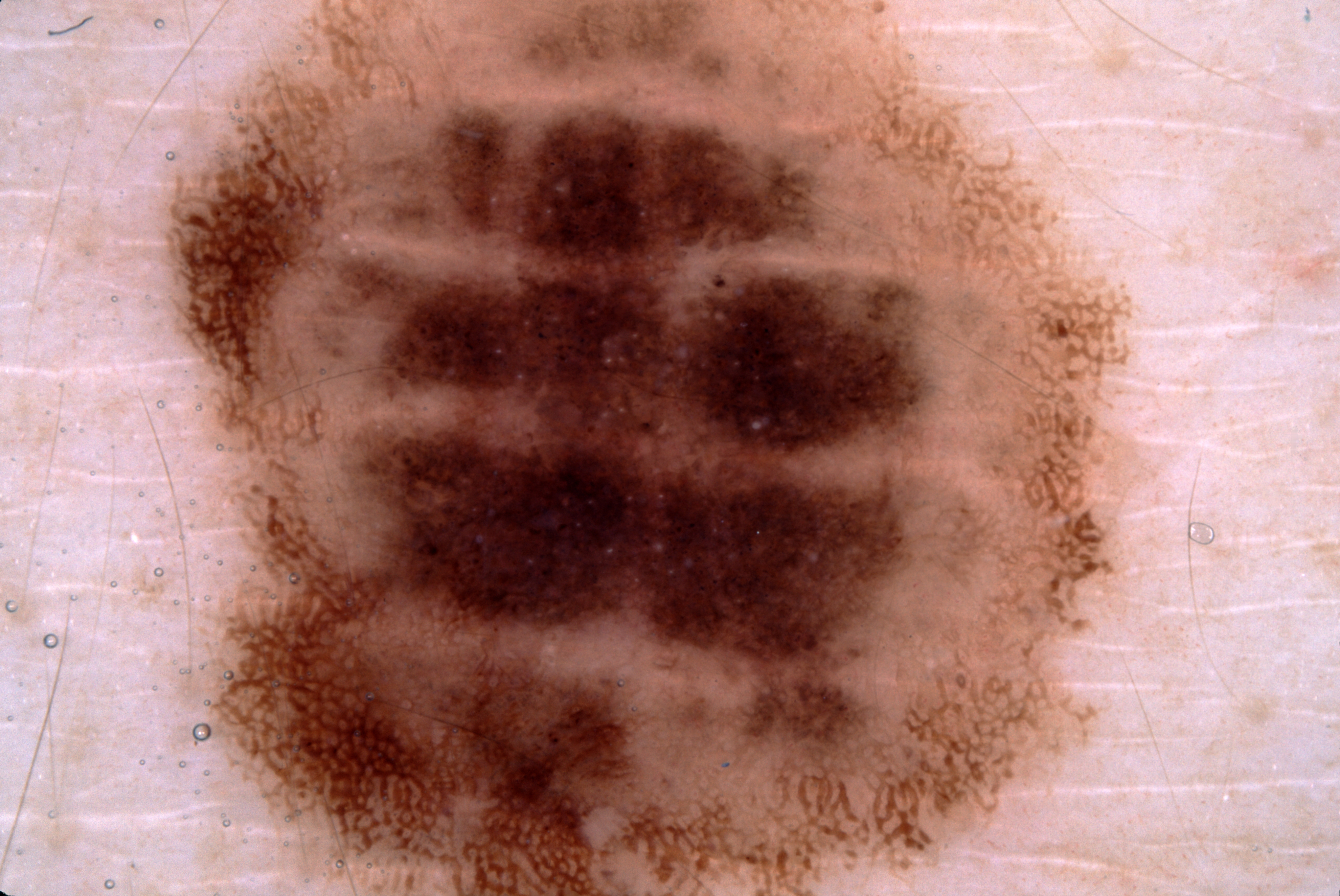This is a dermoscopic photograph of a skin lesion.
The subject is a female aged approximately 25.
Dermoscopic assessment notes pigment network and milia-like cysts, with no streaks or negative network.
The visible lesion spans [167, 0, 1151, 895].
The diagnostic assessment was a melanocytic nevus, a benign skin lesion.